A skin lesion imaged with a dermatoscope.
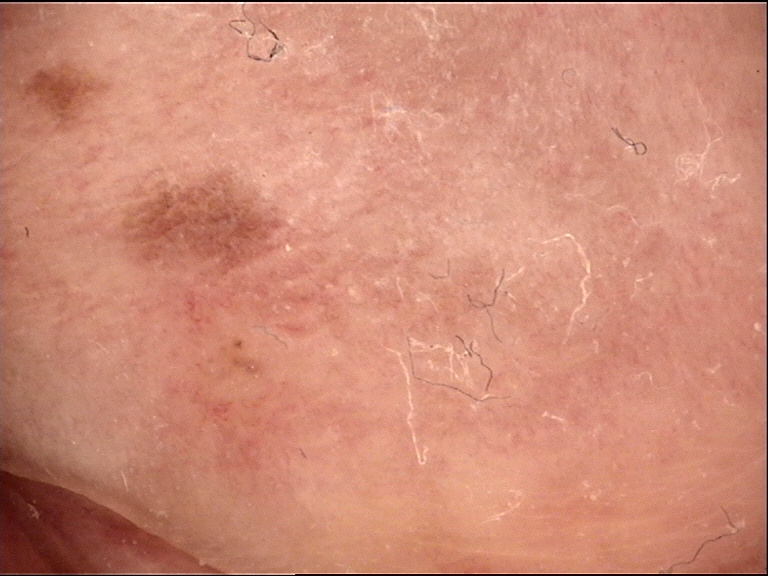Consistent with a benign lesion — a dysplastic junctional nevus.